Located on the arm and leg · the photograph is a close-up of the affected area · the contributor is female.
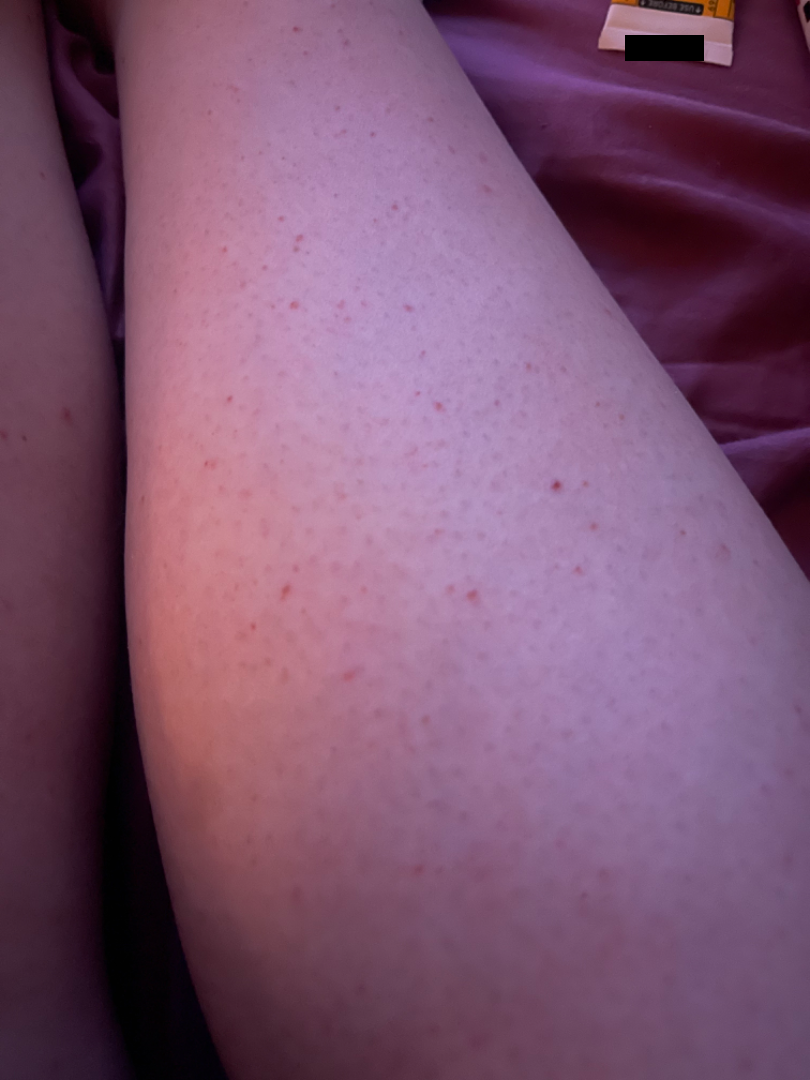Q: Could the case be diagnosed?
A: ungradable on photographic review
Q: When did this start?
A: less than one week
Q: Constitutional symptoms?
A: none reported
Q: What symptoms does the patient report?
A: itching
Q: How does the lesion feel?
A: raised or bumpy
Q: Patient's own categorization?
A: a rash